A dermatoscopic image of a skin lesion.
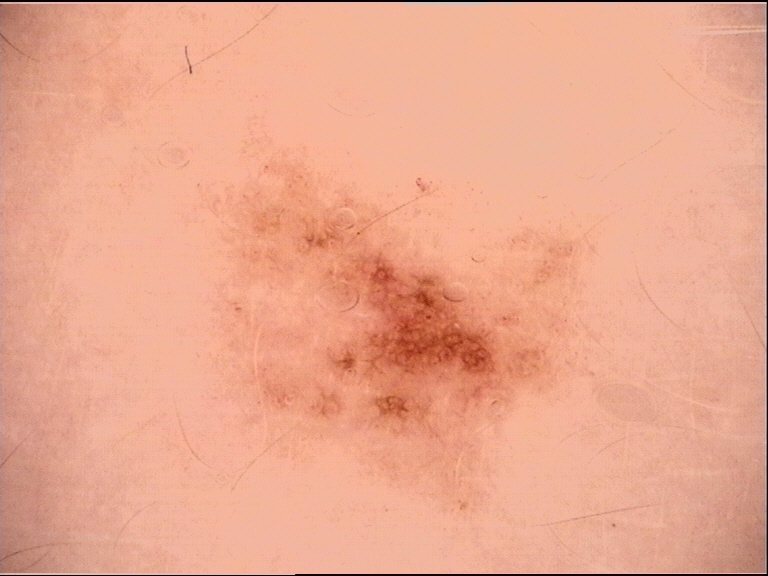<case>
  <diagnosis>
    <name>dysplastic junctional nevus</name>
    <code>jd</code>
    <malignancy>benign</malignancy>
    <super_class>melanocytic</super_class>
    <confirmation>expert consensus</confirmation>
  </diagnosis>
</case>